The contributor is a male aged 30–39, the photograph is a close-up of the affected area, the back of the torso is involved — 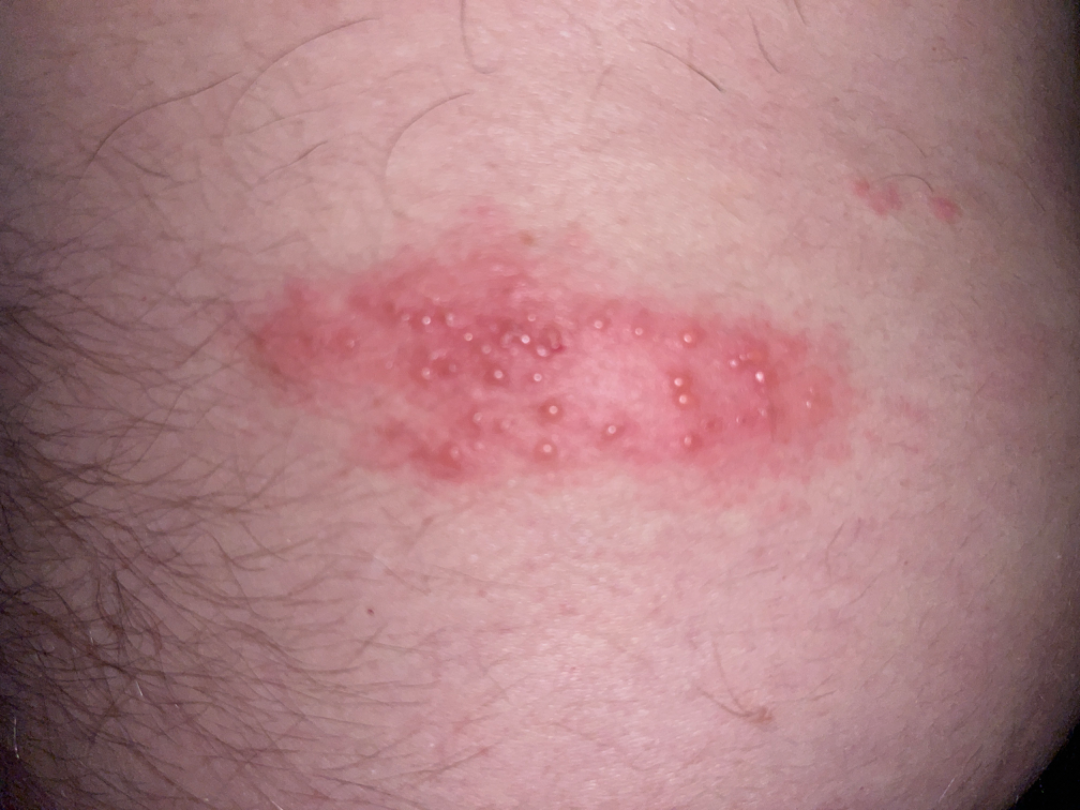The condition has been present for less than one week. Self-categorized by the patient as a rash. The contributor reports the lesion is raised or bumpy. The patient reported no systemic symptoms. The contributor reports enlargement, bothersome appearance and itching. Favoring Herpes Zoster.